Numerous moles by the patient's own estimate · the patient says their skin tans without first burning · a dermoscopic image of a skin lesion · acquired for a research image collection, with no referral diagnosis · by self-report, no personal history of cancer · a female subject 78 years of age:
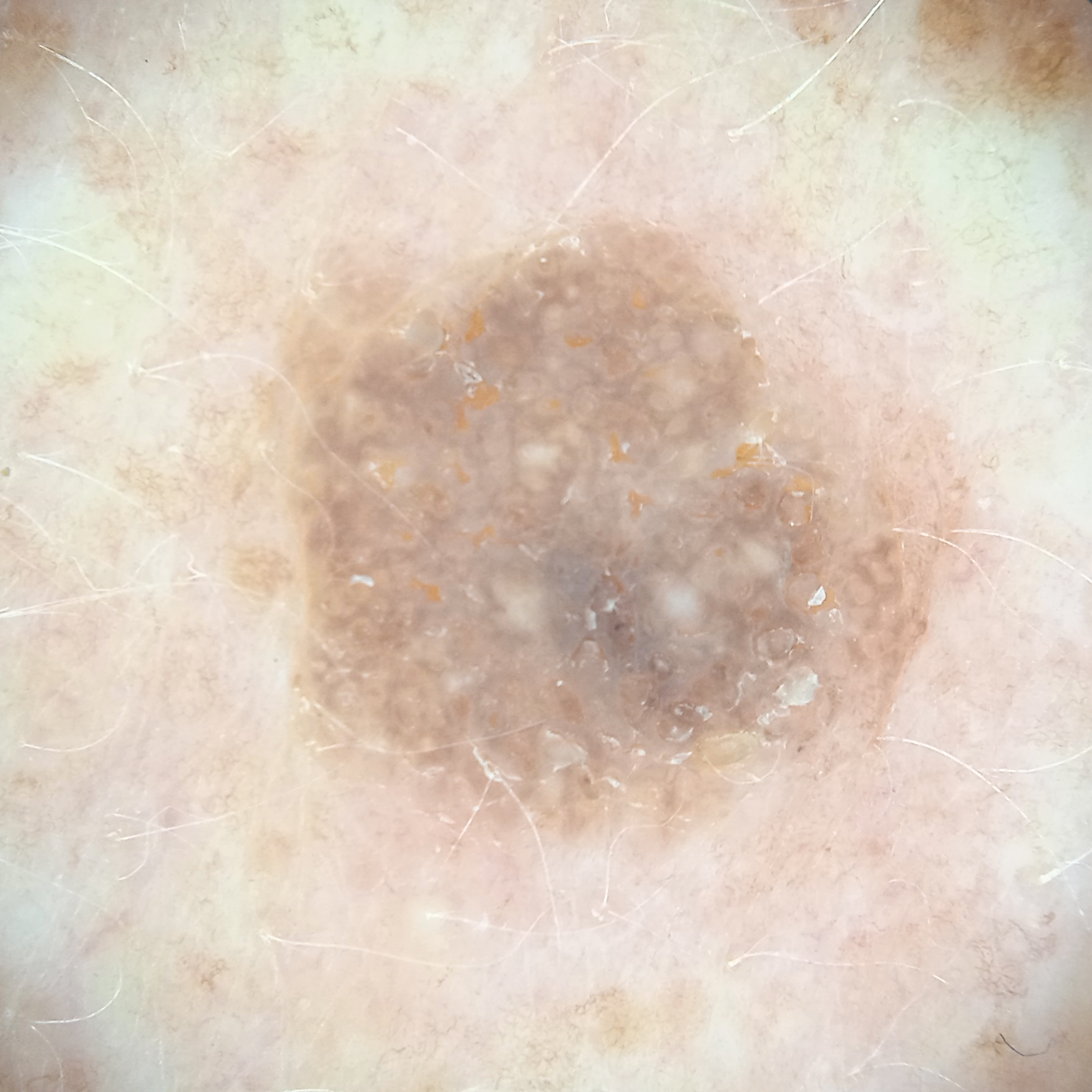The lesion involves the back. Measuring roughly 7.3 mm. The diagnostic impression was a seborrheic keratosis.